Skin tone: human graders estimated Monk skin tone scale 2 or 3; the photo was captured at an angle: 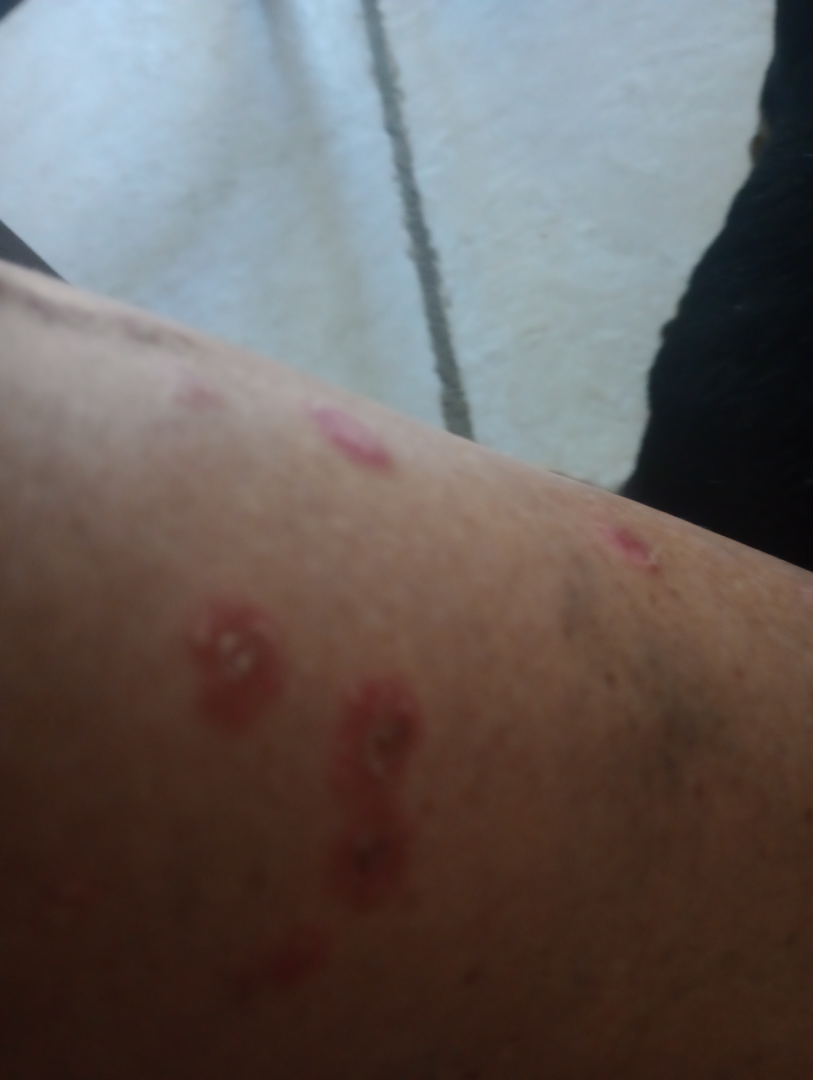Impression:
The skin findings could not be characterized from the image.